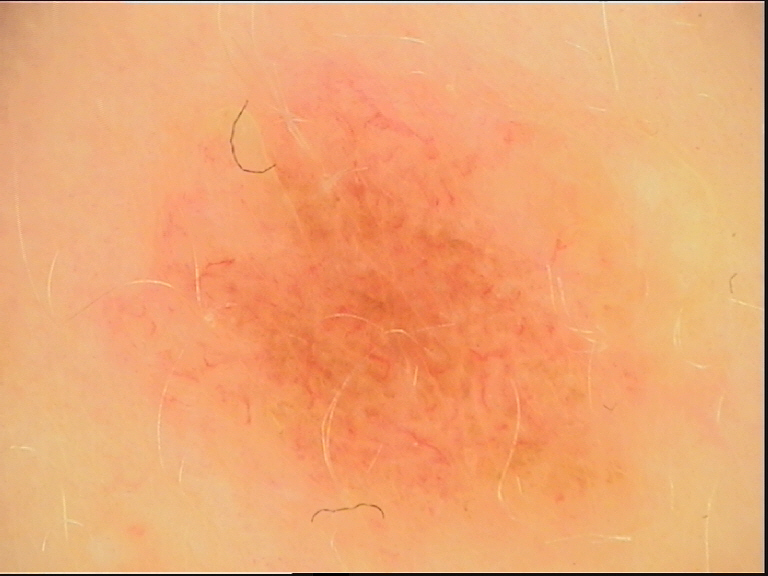image: dermatoscopy
diagnosis:
  name: dysplastic compound nevus
  code: cd
  malignancy: benign
  super_class: melanocytic
  confirmation: expert consensus